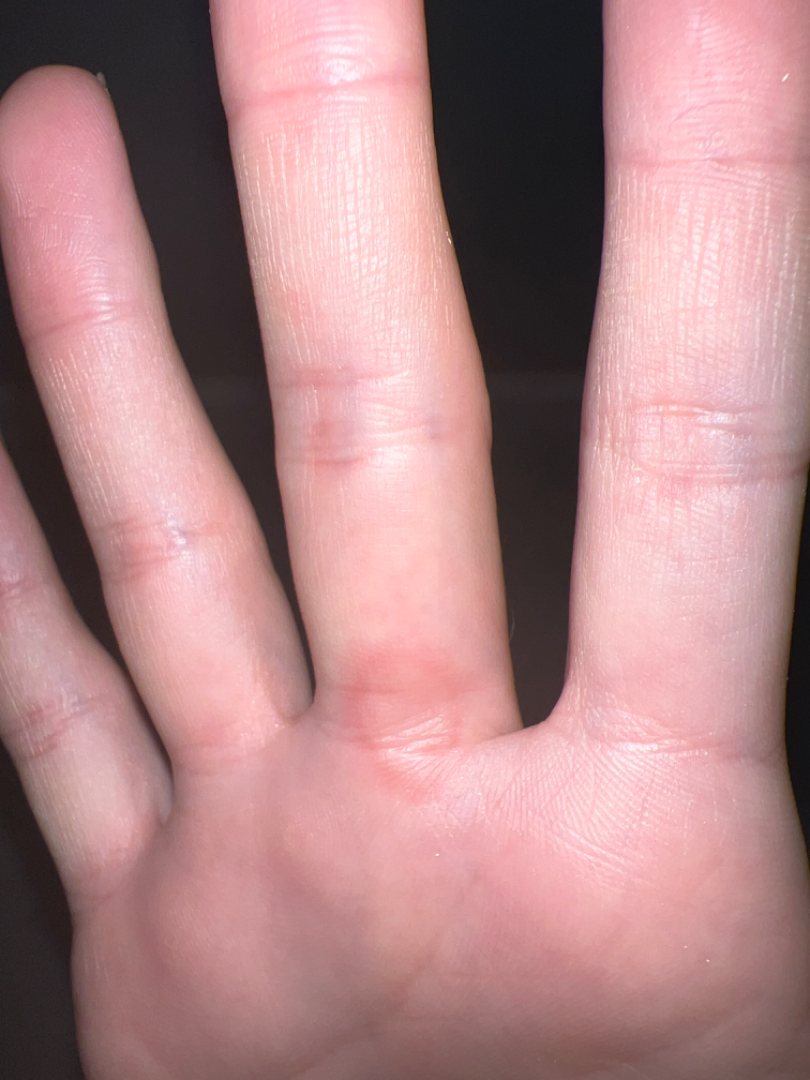On teledermatology review: Viral Exanthem, Erythema multiforme and Drug Rash were each considered, in no particular order.